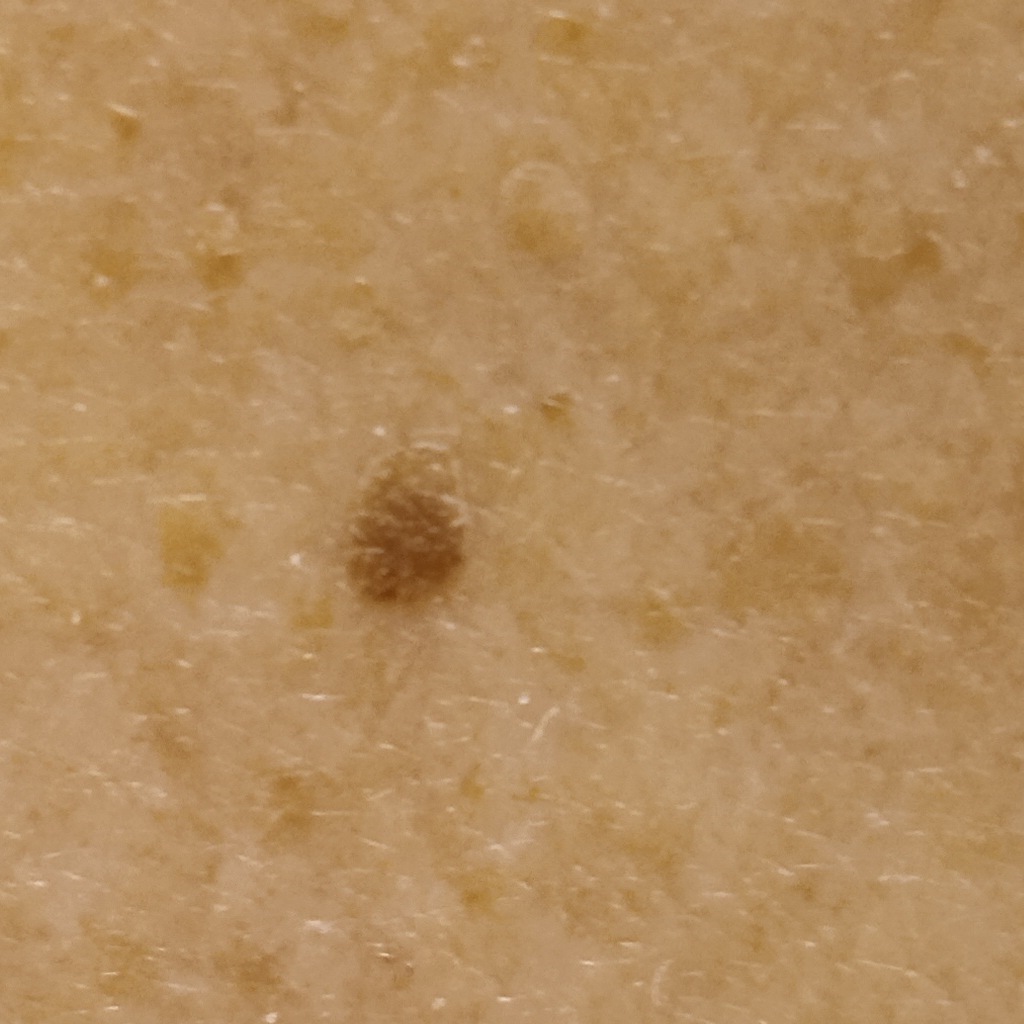Assessment: The diagnostic impression was a seborrheic keratosis.